A skin lesion imaged with a dermatoscope.
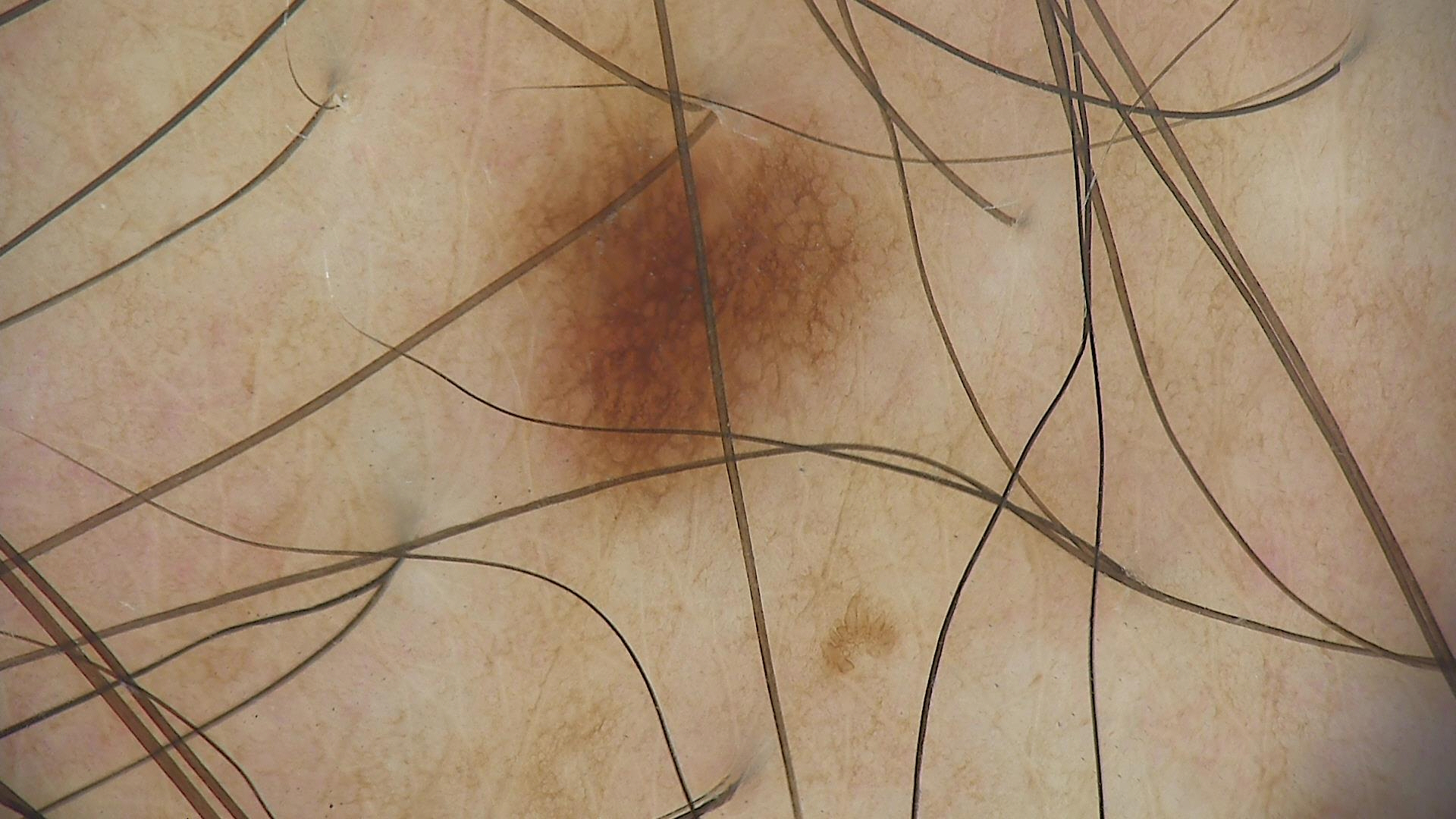The diagnostic label was a benign lesion — a dysplastic junctional nevus.